A dermoscopy image of a single skin lesion; a female patient aged approximately 70:
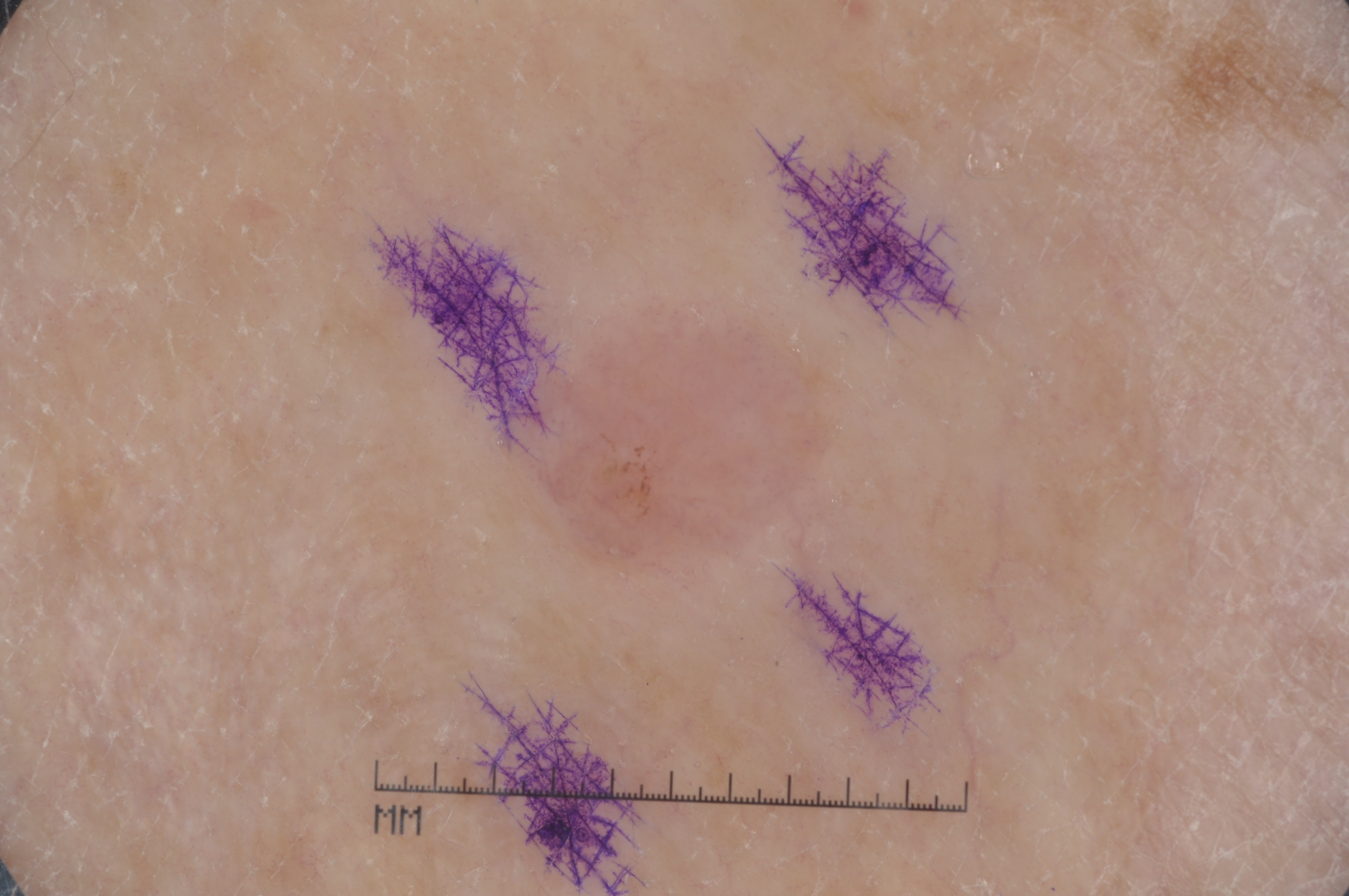{
  "lesion_extent": "small",
  "dermoscopic_features": {
    "present": [
      "pigment network"
    ],
    "absent": [
      "milia-like cysts",
      "streaks",
      "negative network"
    ]
  },
  "lesion_location": {
    "bbox_xyxy": [
      513,
      281,
      863,
      581
    ]
  },
  "diagnosis": {
    "name": "melanocytic nevus",
    "malignancy": "benign",
    "lineage": "melanocytic",
    "provenance": "clinical"
  }
}